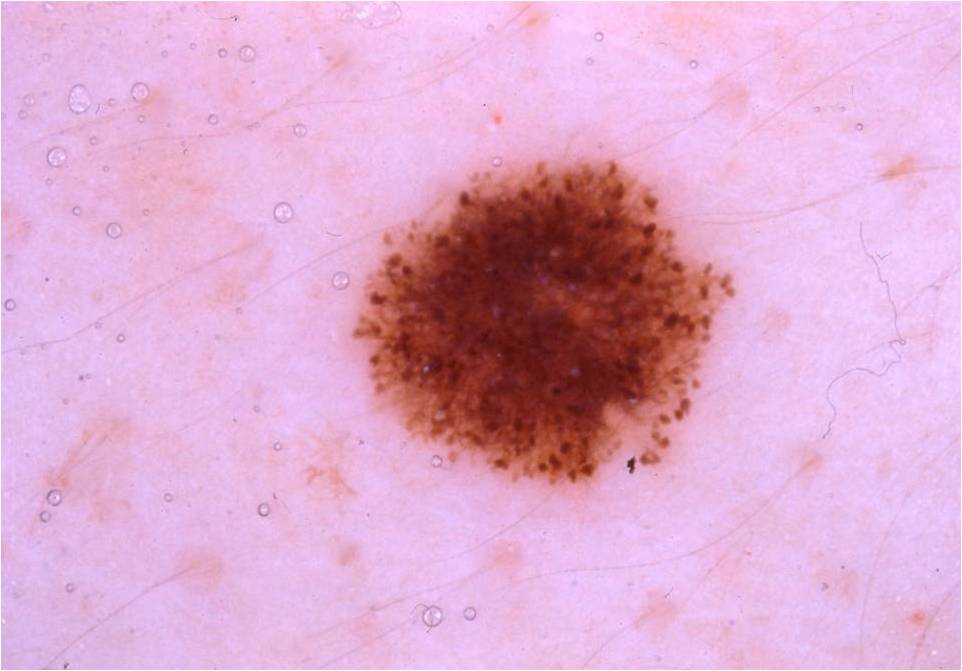Summary:
Dermoscopy of a skin lesion. The patient is a female aged approximately 30. As (left, top, right, bottom), the lesion spans <bbox>350, 153, 745, 489</bbox>. Dermoscopic assessment notes globules and pigment network, with no negative network, milia-like cysts, or streaks.
Conclusion:
Expert review diagnosed this as a melanocytic nevus.